Reported duration is less than one week · texture is reported as rough or flaky and raised or bumpy · located on the arm · the photo was captured at an angle · Fitzpatrick II; human graders estimated Monk Skin Tone 2 (US pool) or 3 (India pool) · the patient considered this a rash:
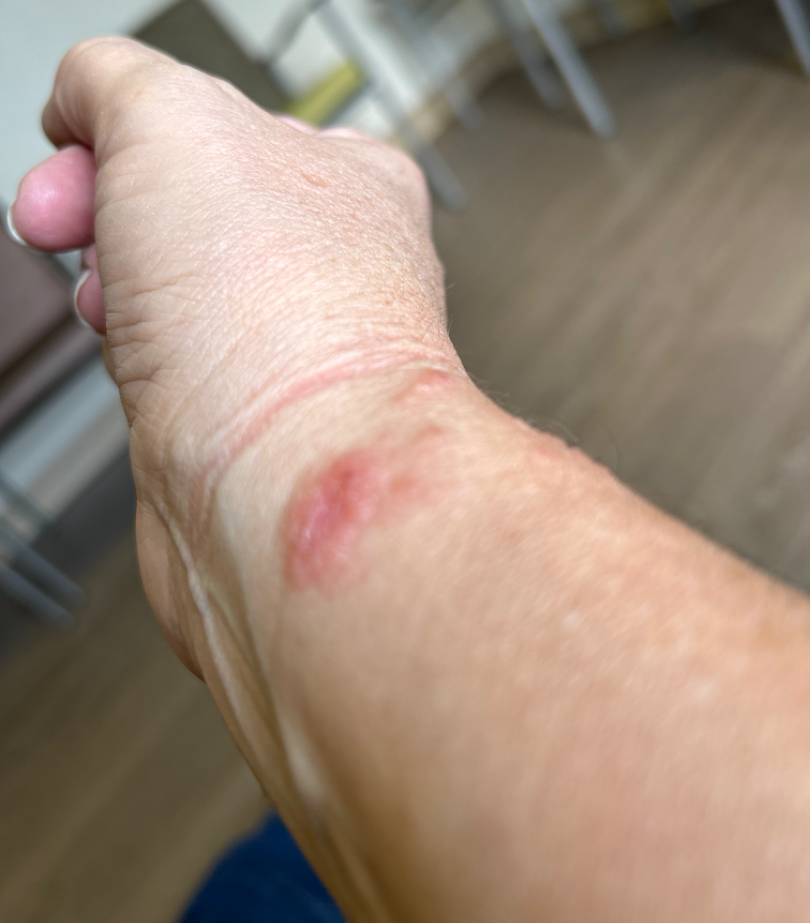The case was indeterminate on photographic review.